A dermatoscopic image of a skin lesion.
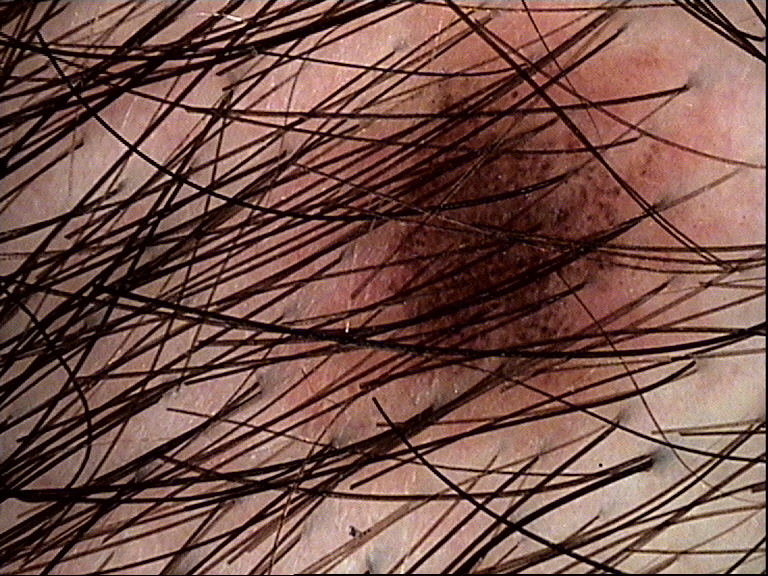Impression:
The diagnostic label was a dysplastic junctional nevus.